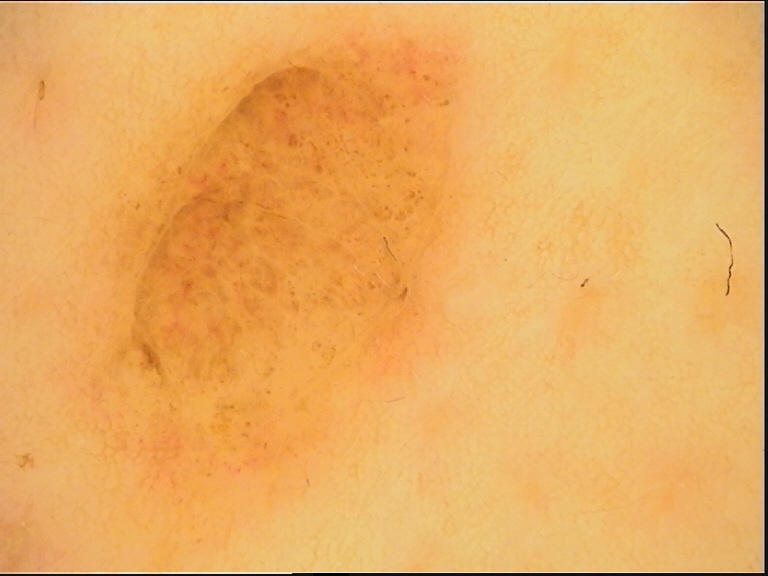class = compound nevus (expert consensus).